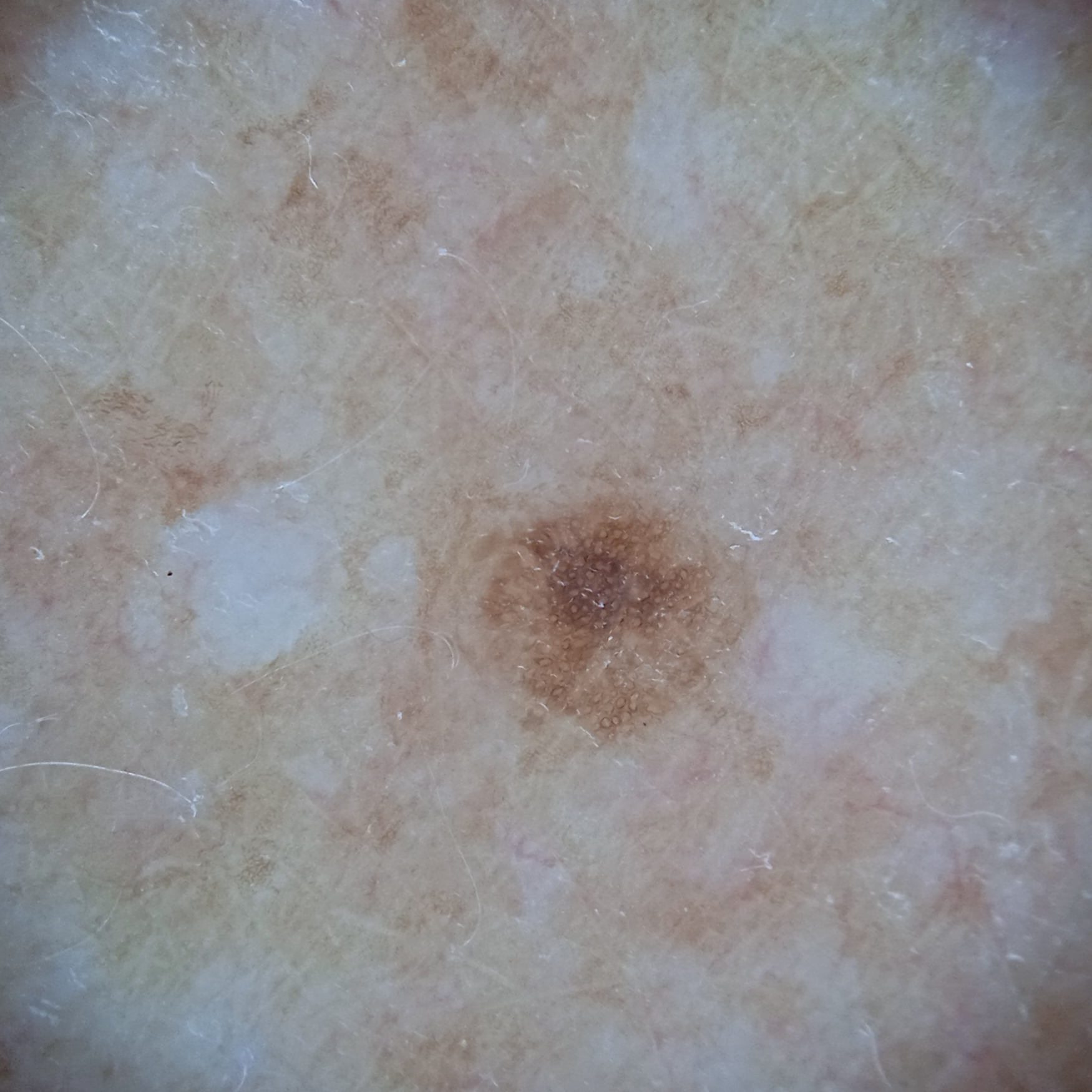Findings:
A dermoscopy image of a skin lesion. A moderate number of moles by the patient's own estimate. On a questionnaire the patient reported a personal history of skin cancer and a personal history of cancer. The lesion measures approximately 2.7 mm.
Assessment:
The diagnostic impression was a melanocytic nevus.